The chart records prior skin cancer (patient or family), pesticide exposure, and prior malignancy (patient or family) · a clinical photograph showing a skin lesion · a female patient in their late 50s:
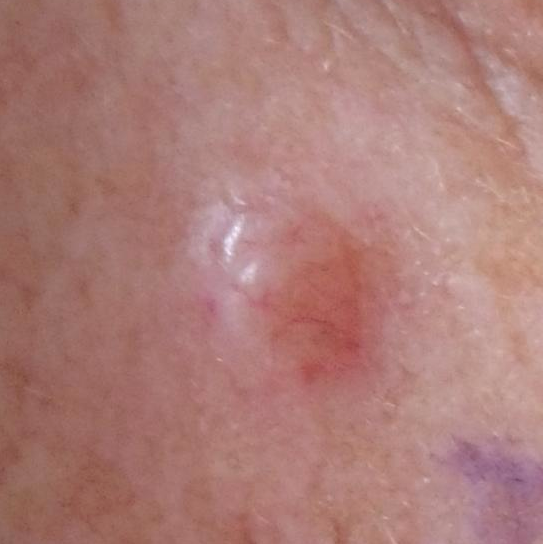Patient and lesion:
Located on the face. The lesion is roughly 5 by 4 mm. By the patient's account, the lesion itches and is elevated.
Conclusion:
Histopathological examination showed a basal cell carcinoma.